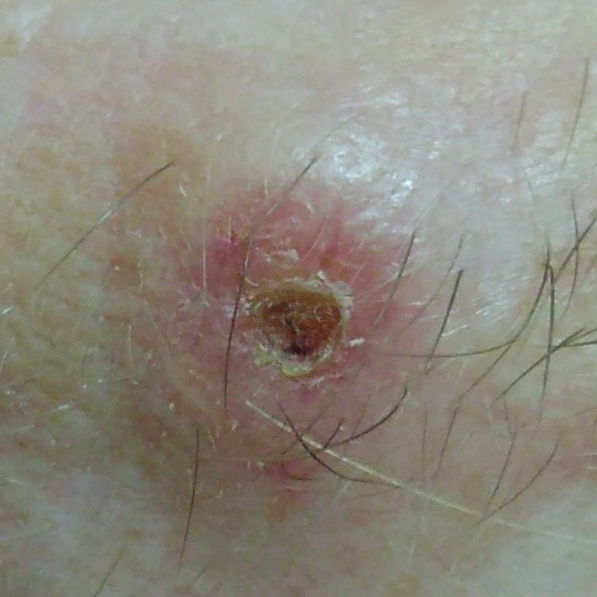The chart records prior malignancy (patient or family) and no pesticide exposure. A clinical close-up photograph of a skin lesion. A female subject in their 80s. The patient was assessed as Fitzpatrick II. Histopathological examination showed a skin cancer — a squamous cell carcinoma.